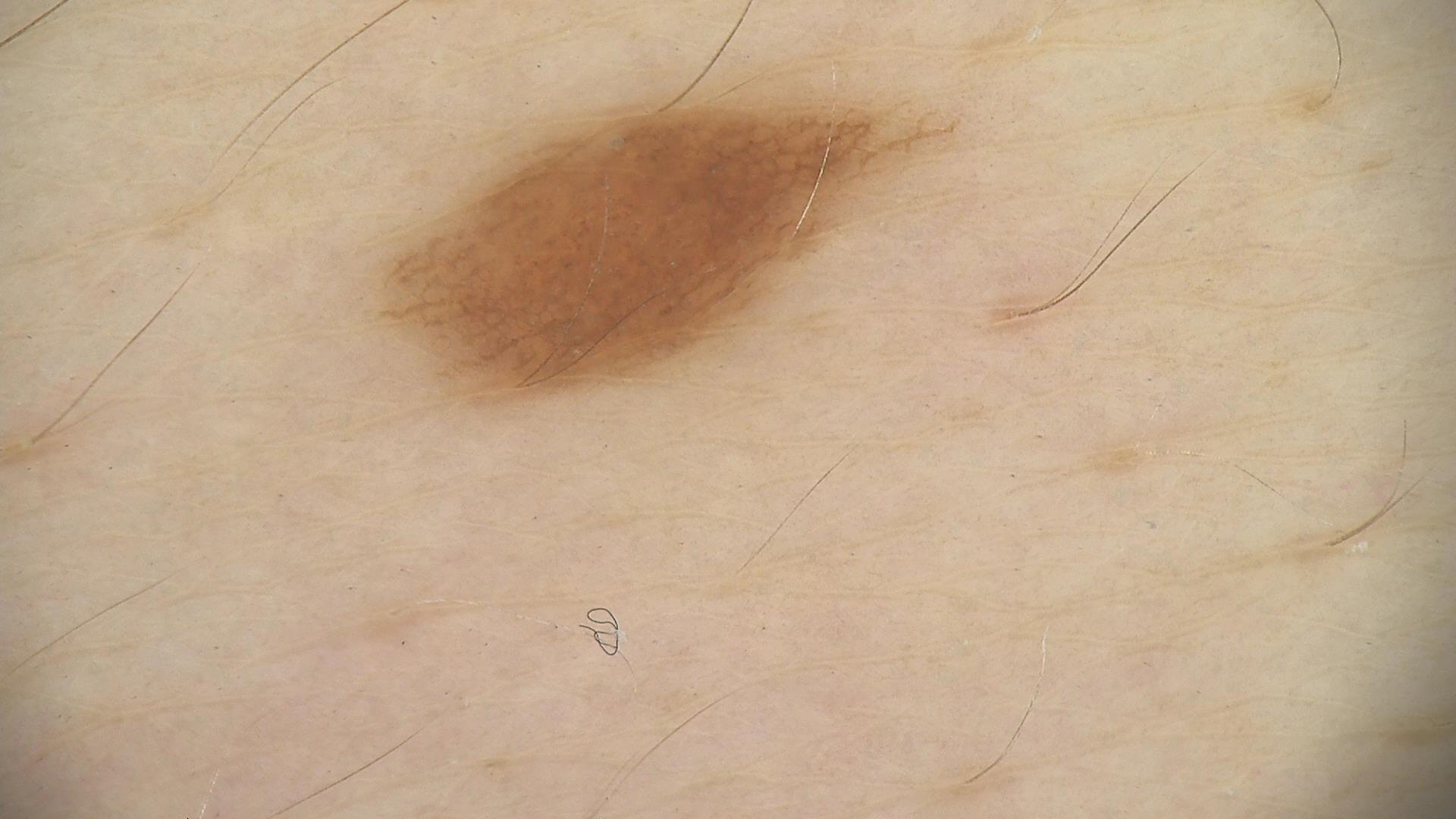A dermoscopic image of a skin lesion.
This is a banal lesion.
Consistent with a junctional nevus.